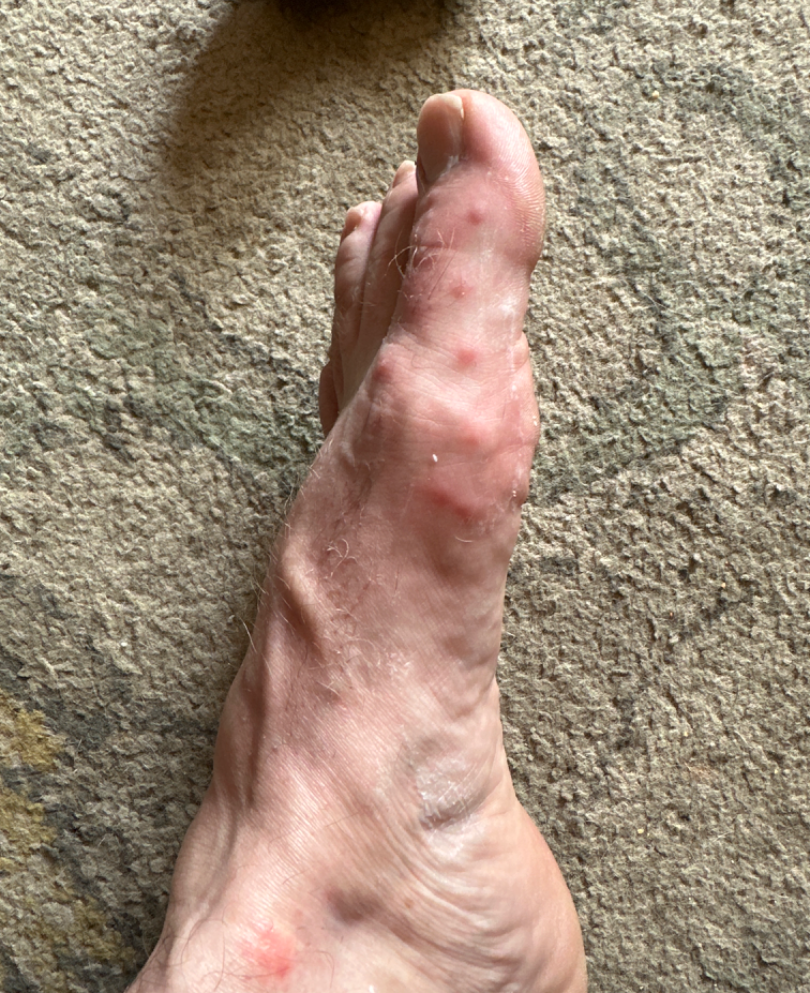differential:
  Insect Bite: 1.0